The head or neck, back of the torso, arm and leg are involved · this is a close-up image: 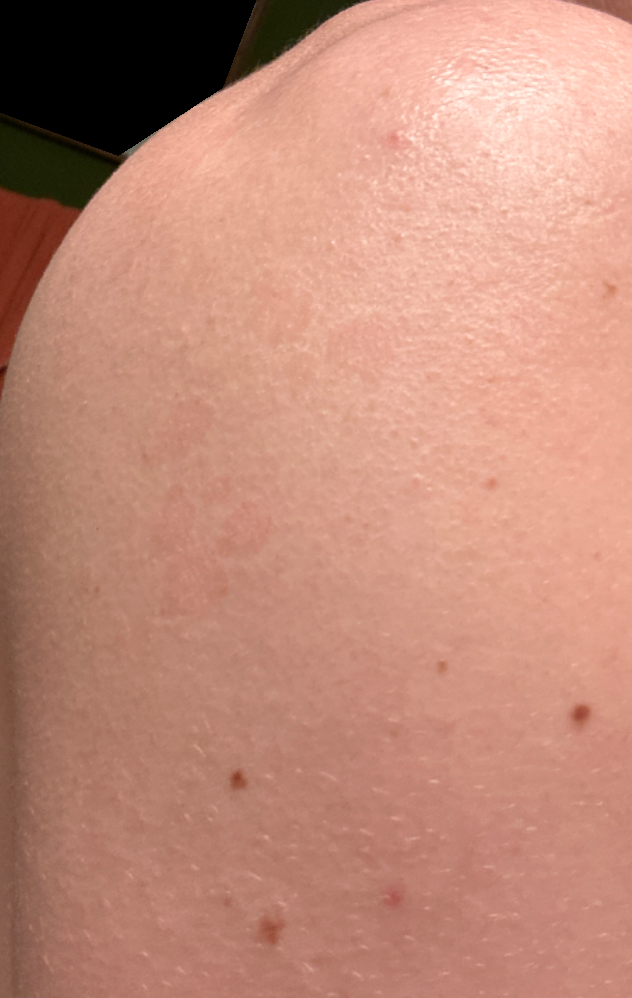| field | value |
|---|---|
| diagnostic considerations | in keeping with Tinea Versicolor |